This is a dermoscopic photograph of a skin lesion · the patient is a male in their 50s: 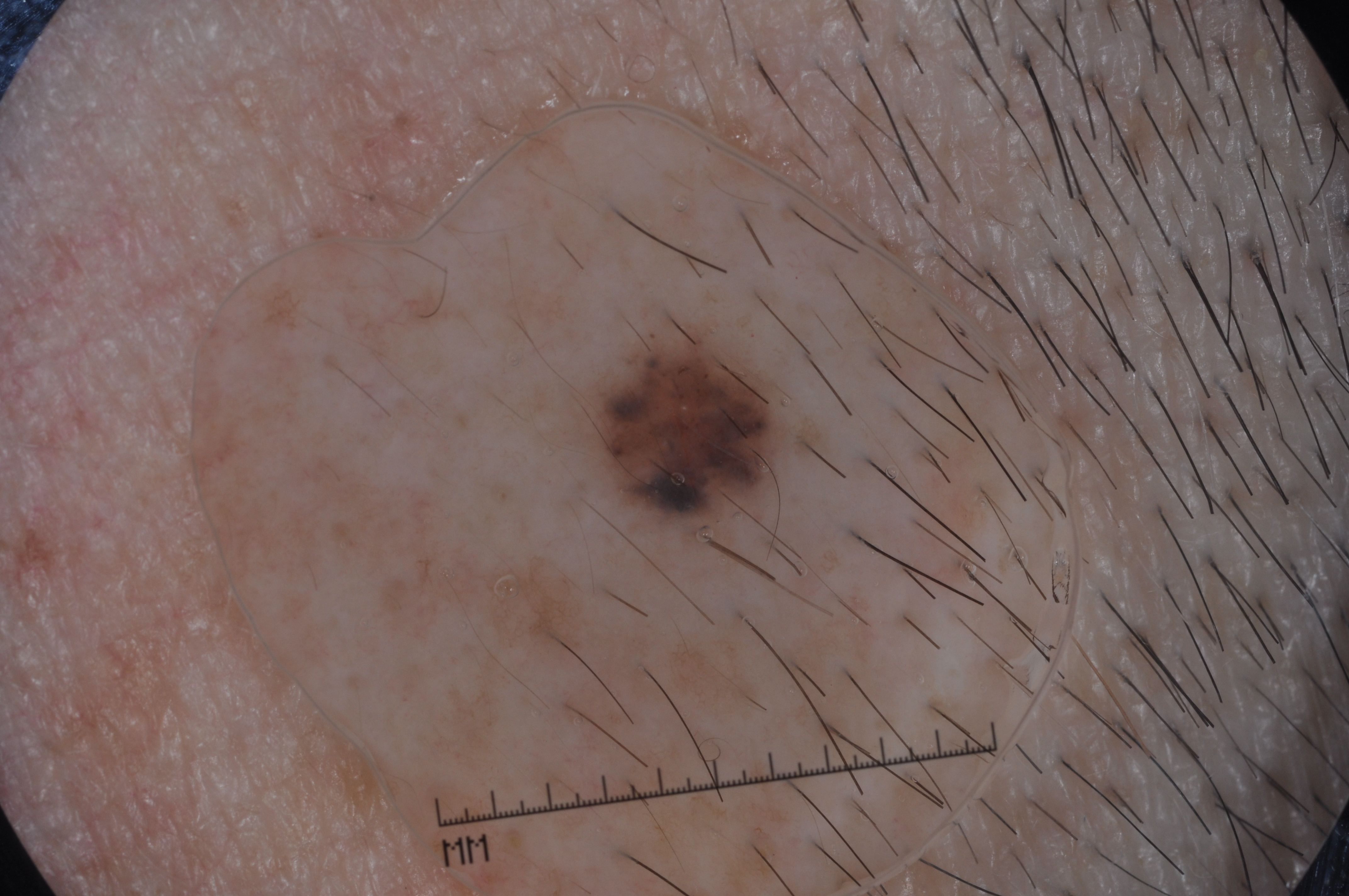Notes:
* dermoscopic features · milia-like cysts; absent: streaks, pigment network, and negative network
* bounding box · (569, 329, 790, 532)
* diagnosis · a melanocytic nevus